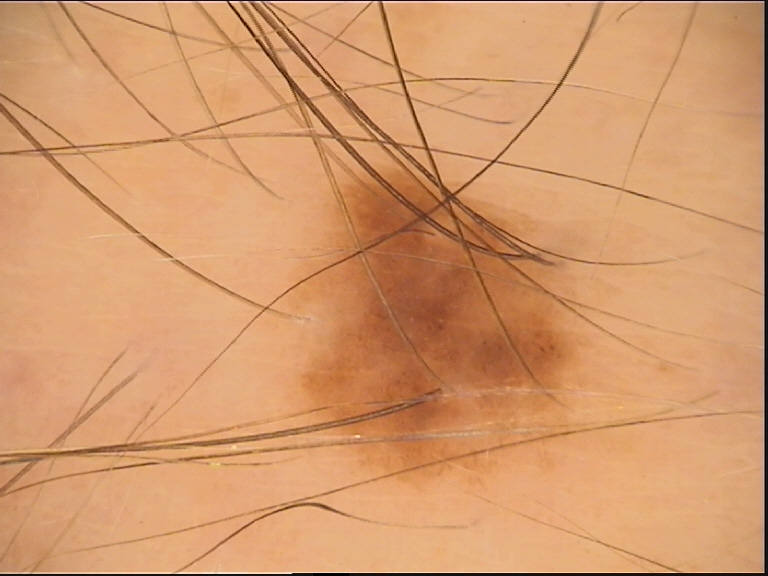Classified as a dysplastic junctional nevus.